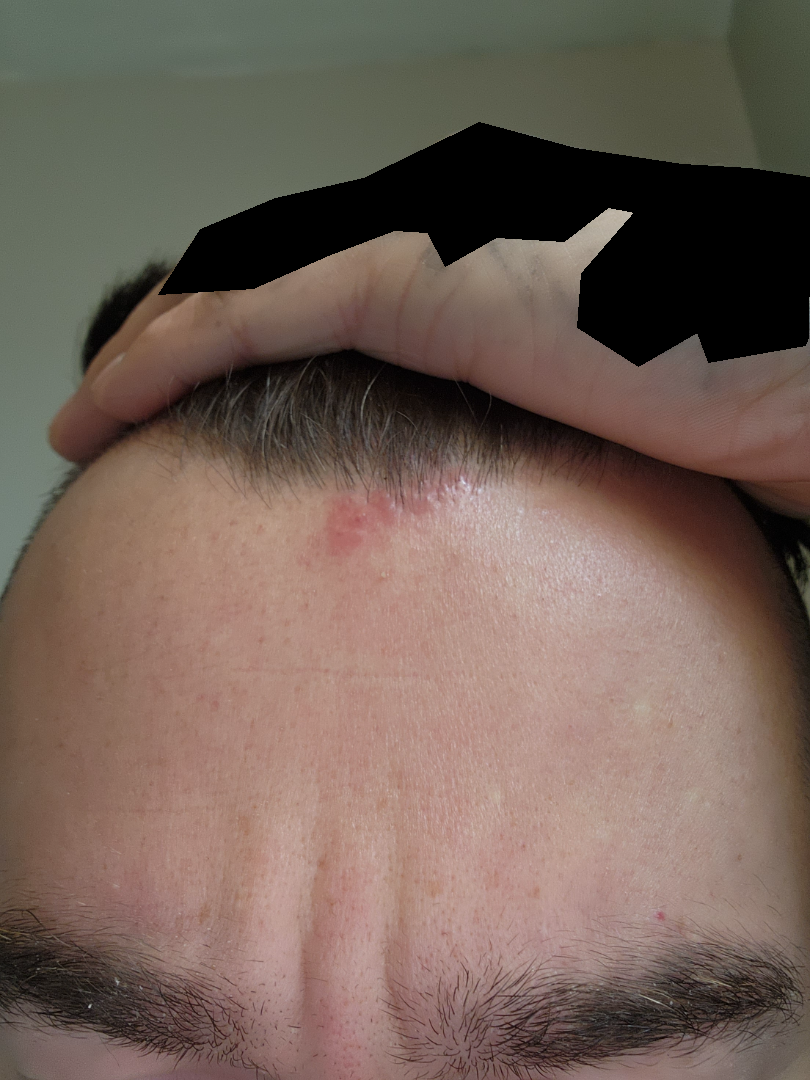assessment: not assessable
body site: head or neck
framing: at a distance